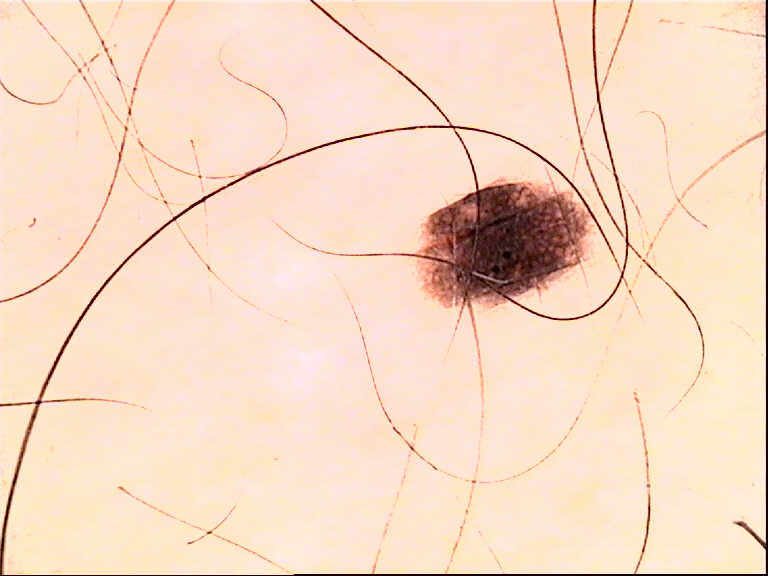label = dysplastic junctional nevus (expert consensus).